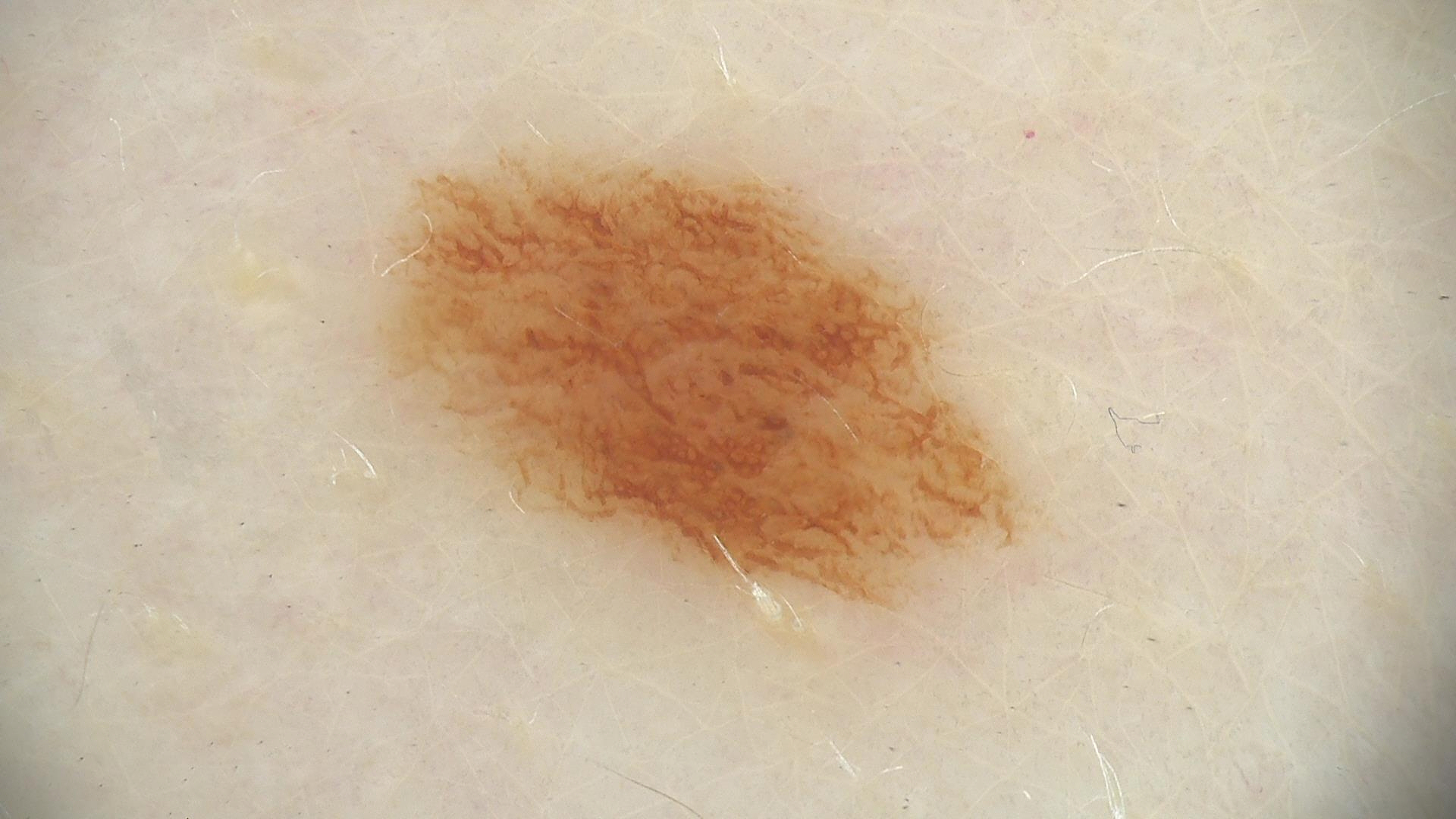image: dermoscopy | label: dysplastic junctional nevus (expert consensus).